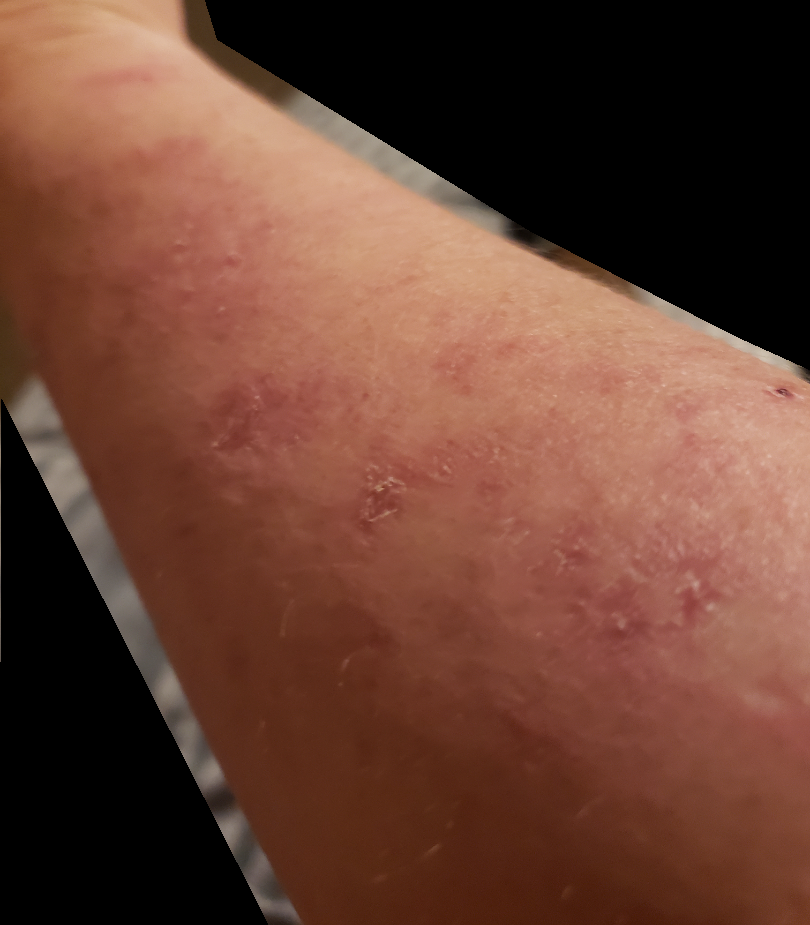Reported duration is one to three months. Female subject, age 40–49. The patient reports bleeding, bothersome appearance and itching. The patient described the issue as a rash. The lesion involves the arm. This is a close-up image. The patient reports the lesion is raised or bumpy and fluid-filled. On independent review by the dermatologists: Eczema (primary); Allergic Contact Dermatitis (possible); Psoriasis (lower probability).